A dermoscopy image of a single skin lesion:
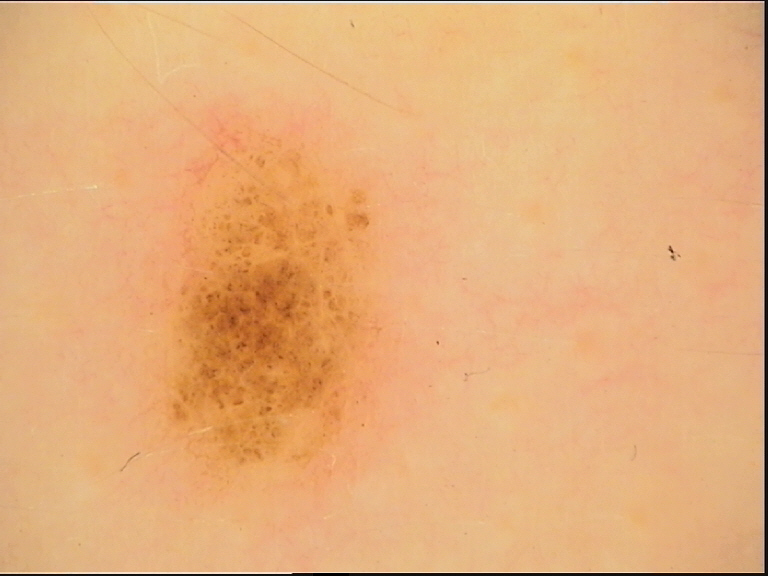Summary:
The architecture is that of a banal lesion.
Conclusion:
Classified as a compound nevus.